A dermoscopy image of a single skin lesion · the subject is a female aged around 10.
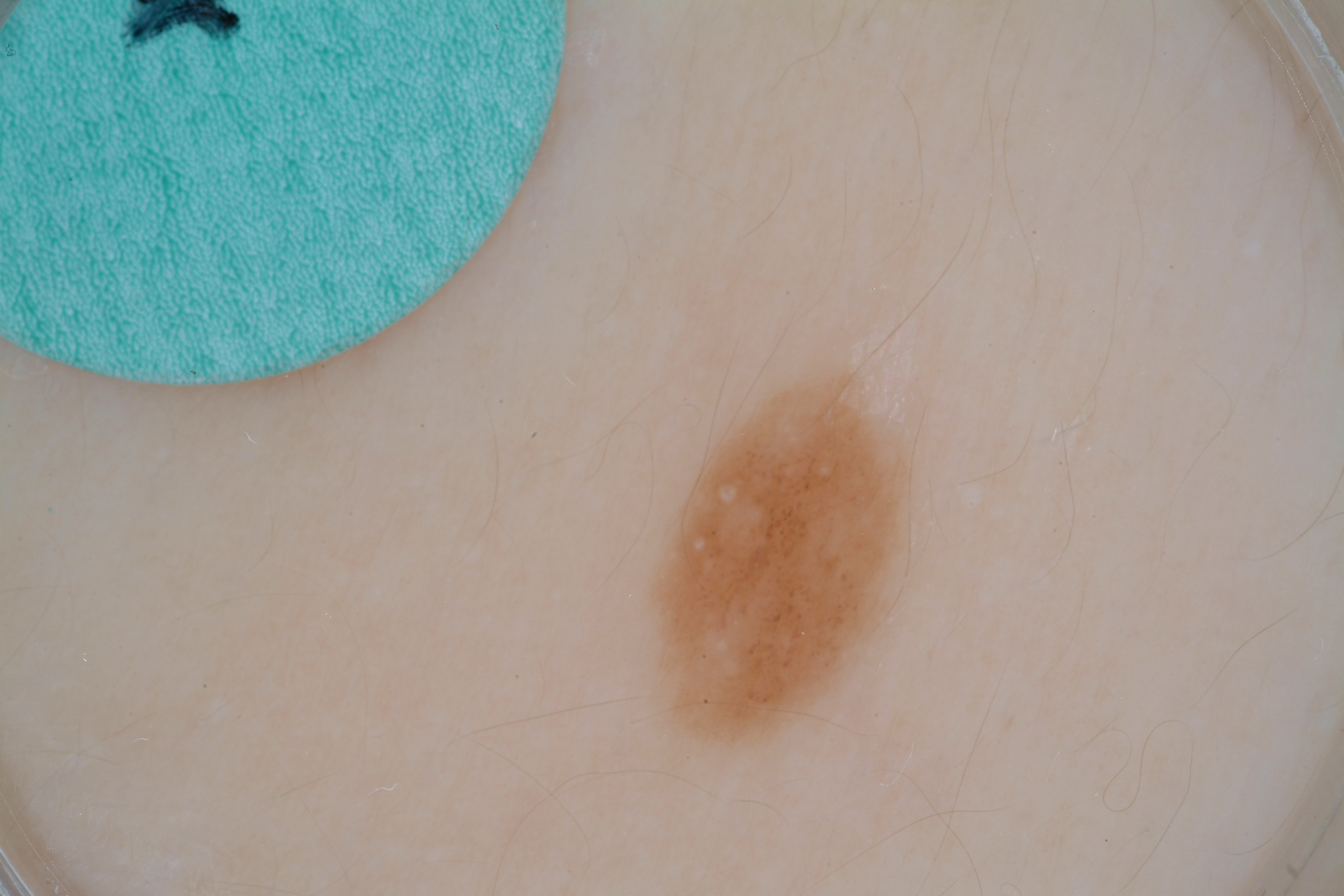| key | value |
|---|---|
| dermoscopic pattern | milia-like cysts and globules |
| extent | small |
| location | 649, 357, 914, 765 |
| impression | a melanocytic nevus, a benign lesion |